A female patient roughly 55 years of age; a skin lesion imaged with contact-polarized dermoscopy: 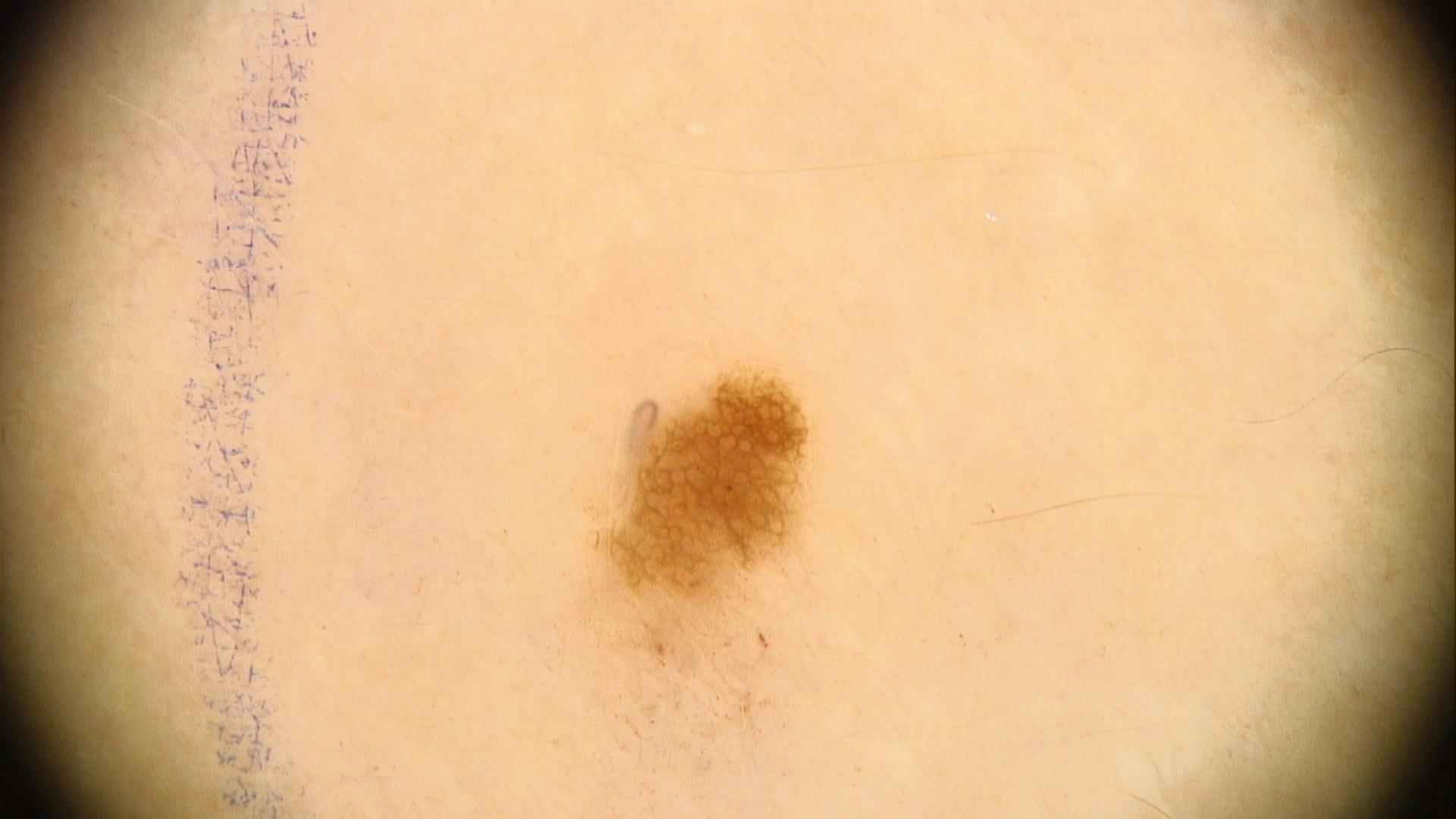| feature | finding |
|---|---|
| site | a lower extremity |
| impression | Nevus |